This image was taken at an angle, the subject is a female aged 18–29, the patient reports itching, reported duration is less than one week, the patient reports the lesion is rough or flaky, located on the leg and arm, the patient described the issue as a rash.
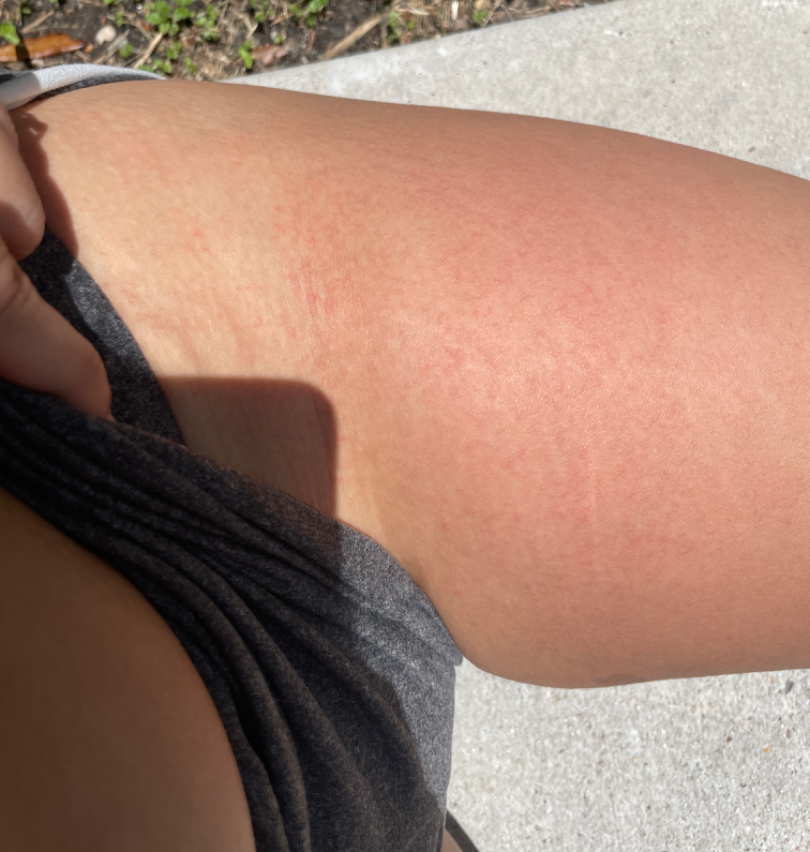Assessment: No clear dermatological pathology was apparent in the photograph.